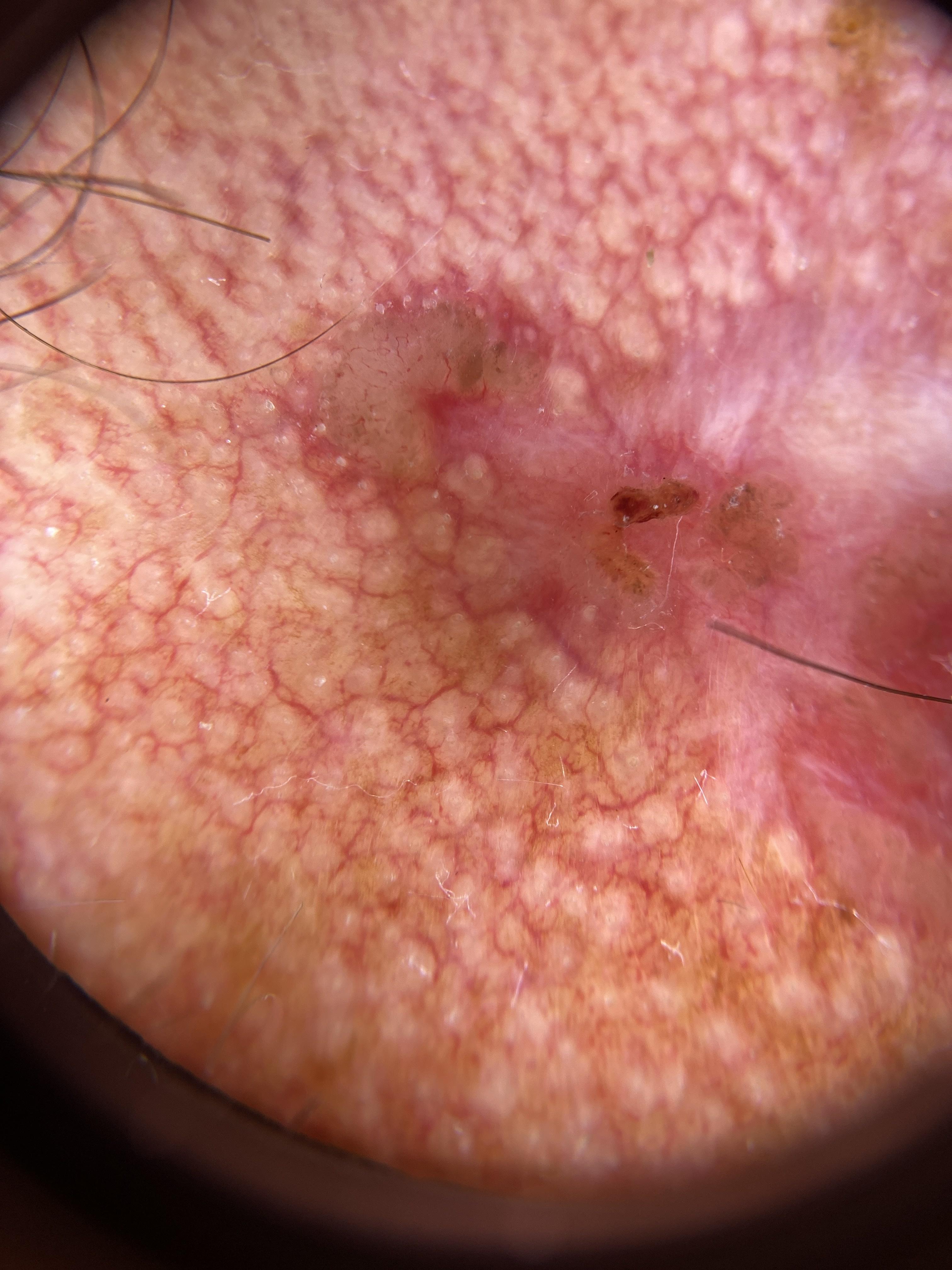diagnosis — Basal cell carcinoma (biopsy-proven).